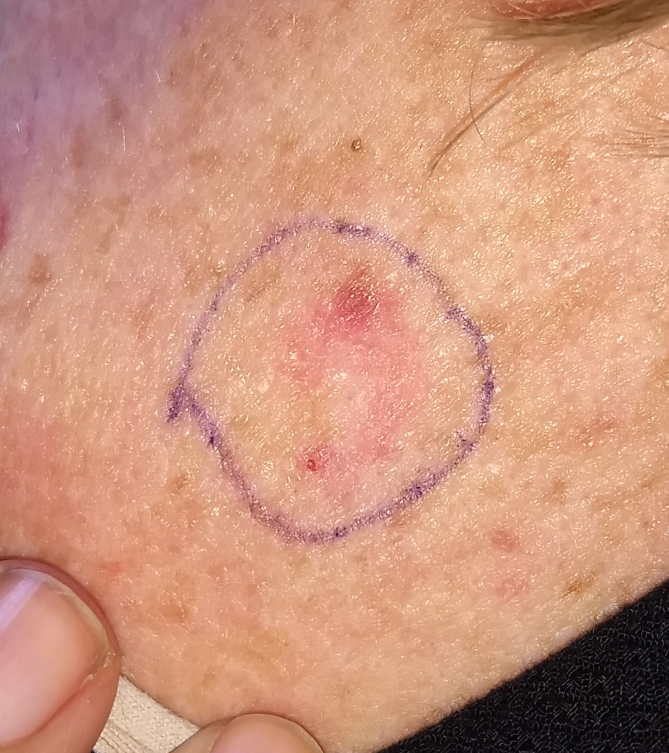| field | value |
|---|---|
| image | clinical photograph |
| skin type | I |
| subject | female, in their early 50s |
| exposures | prior skin cancer (patient or family) |
| location | the back |
| diameter | 12 × 8 mm |
| reported symptoms | none reported |
| diagnostic label | basal cell carcinoma (biopsy-proven) |